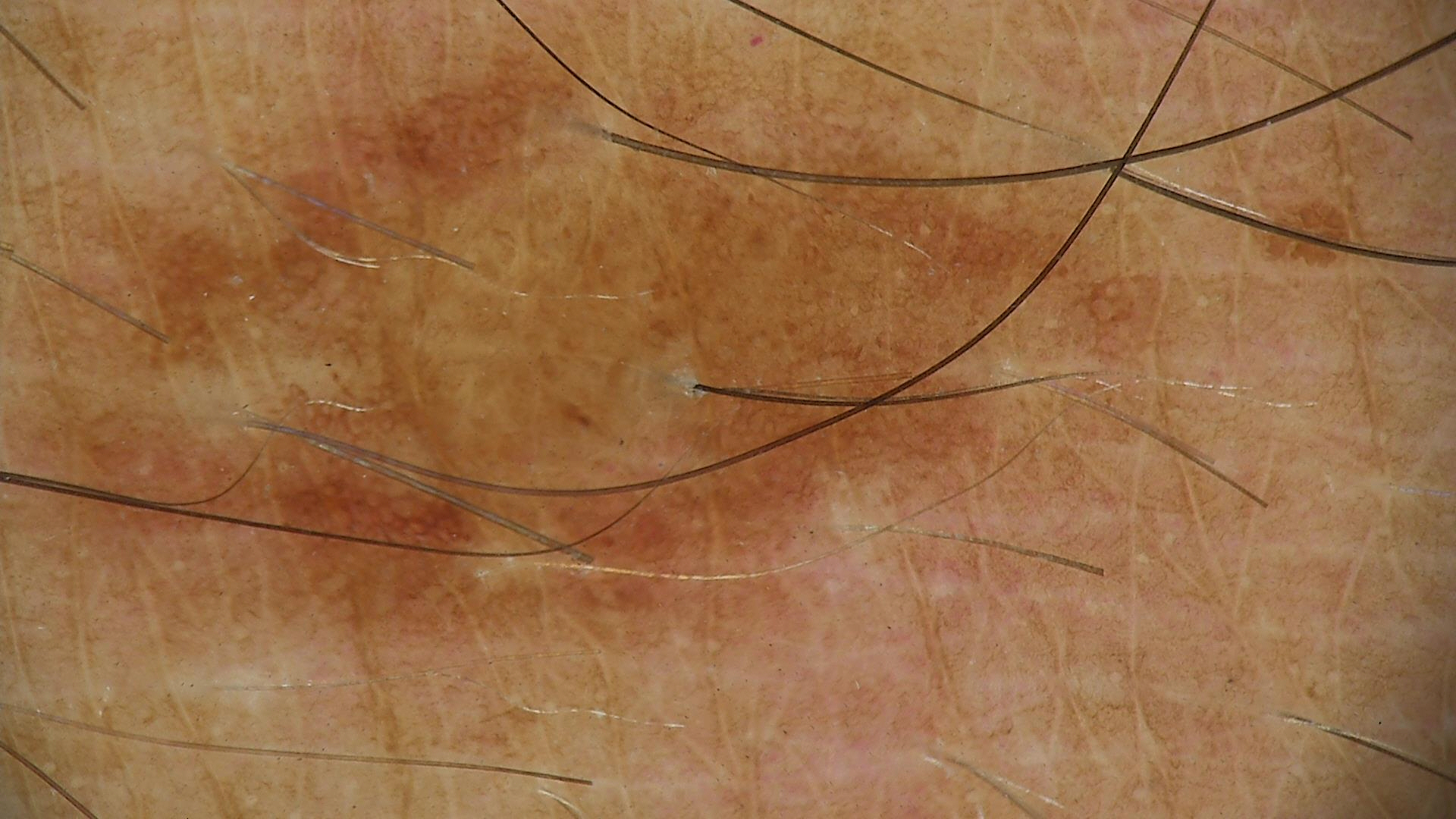Diagnosed as a dysplastic junctional nevus.